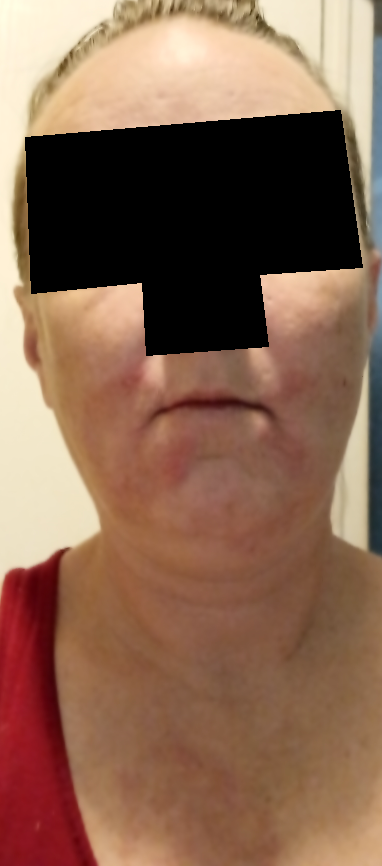Q: What was the assessment?
A: not assessable
Q: How was the photo taken?
A: at a distance
Q: Age and sex?
A: female, age 40–49
Q: Anatomic location?
A: head or neck and front of the torso